A dermatoscopic image of a skin lesion.
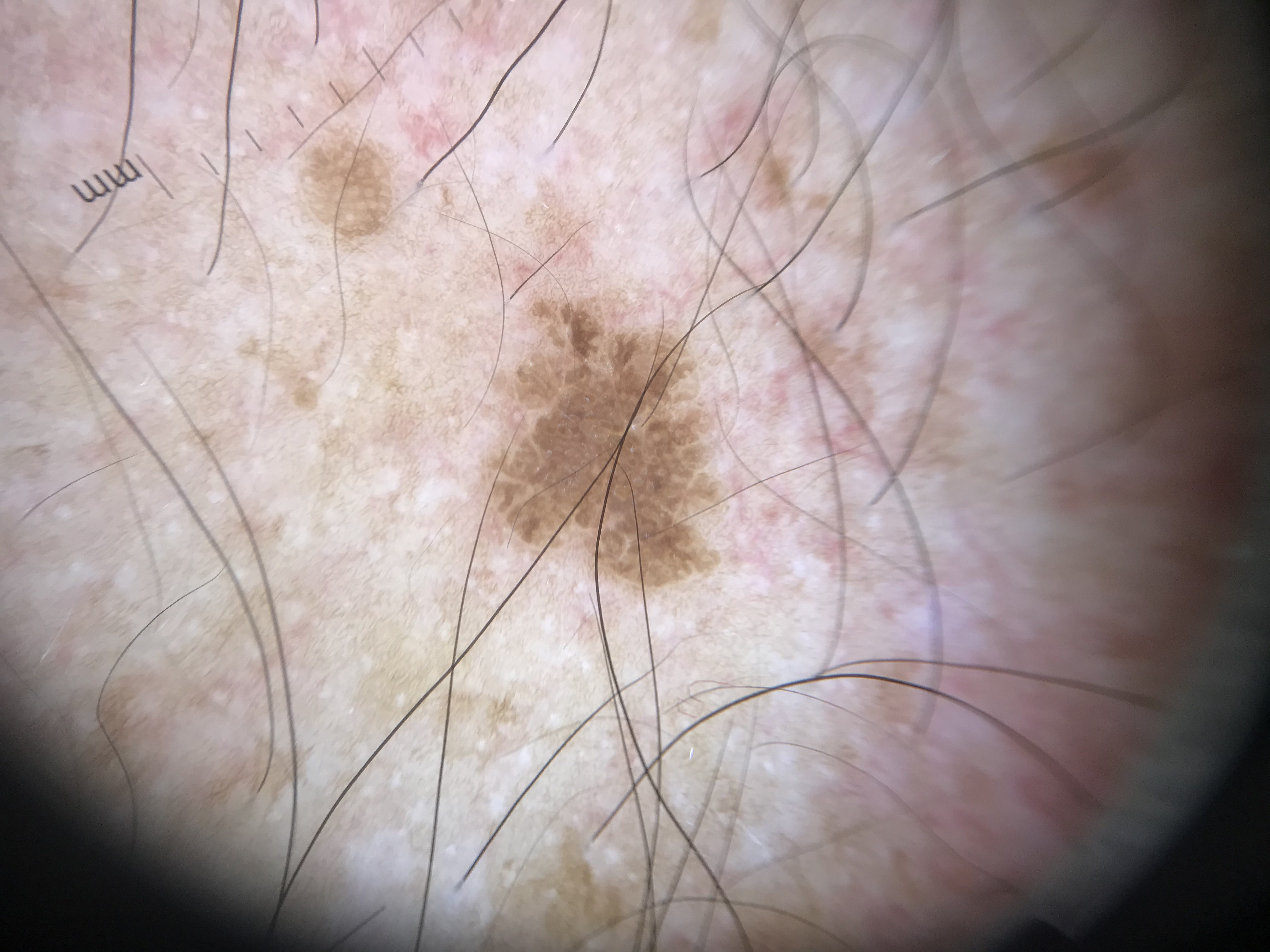The morphology is that of a keratinocytic lesion.
The diagnostic label was a benign lesion — a seborrheic keratosis.